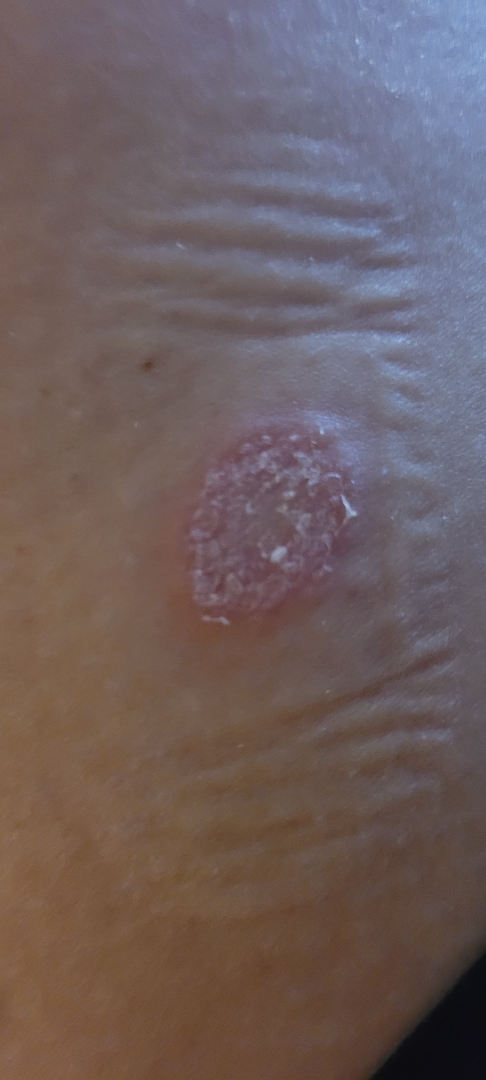{
  "assessment": "indeterminate",
  "body_site": "leg",
  "duration": "less than one week",
  "shot_type": "close-up",
  "texture": [
    "rough or flaky",
    "raised or bumpy"
  ]
}